A skin lesion imaged with a dermatoscope. A male subject, aged approximately 55:
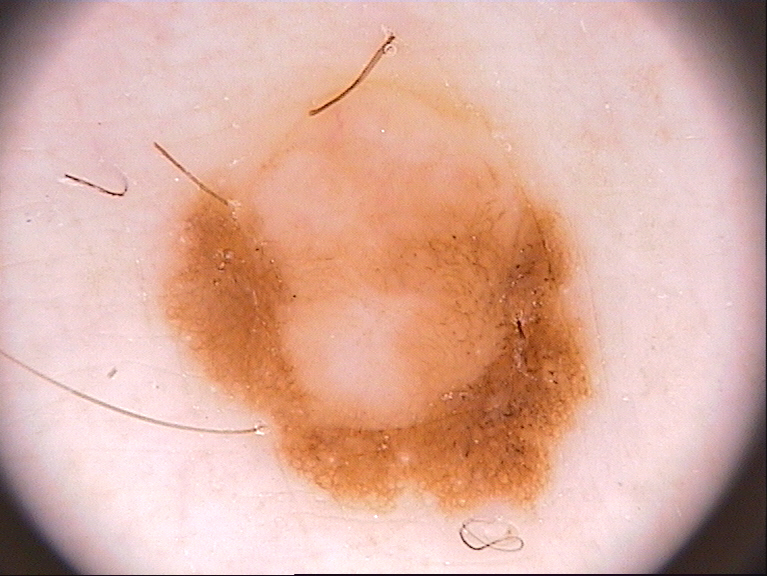Summary: The lesion is located at left=157, top=64, right=604, bottom=524. Dermoscopic review identifies globules and pigment network; no negative network, streaks, or milia-like cysts. Conclusion: The lesion was assessed as a melanocytic nevus, a benign skin lesion.